The lesion is described as fluid-filled and raised or bumpy; the patient is 18–29, female; reported duration is one to four weeks; located on the leg; reported lesion symptoms include itching, bothersome appearance and pain; the patient considered this a rash; close-up view; the patient also reports fever — 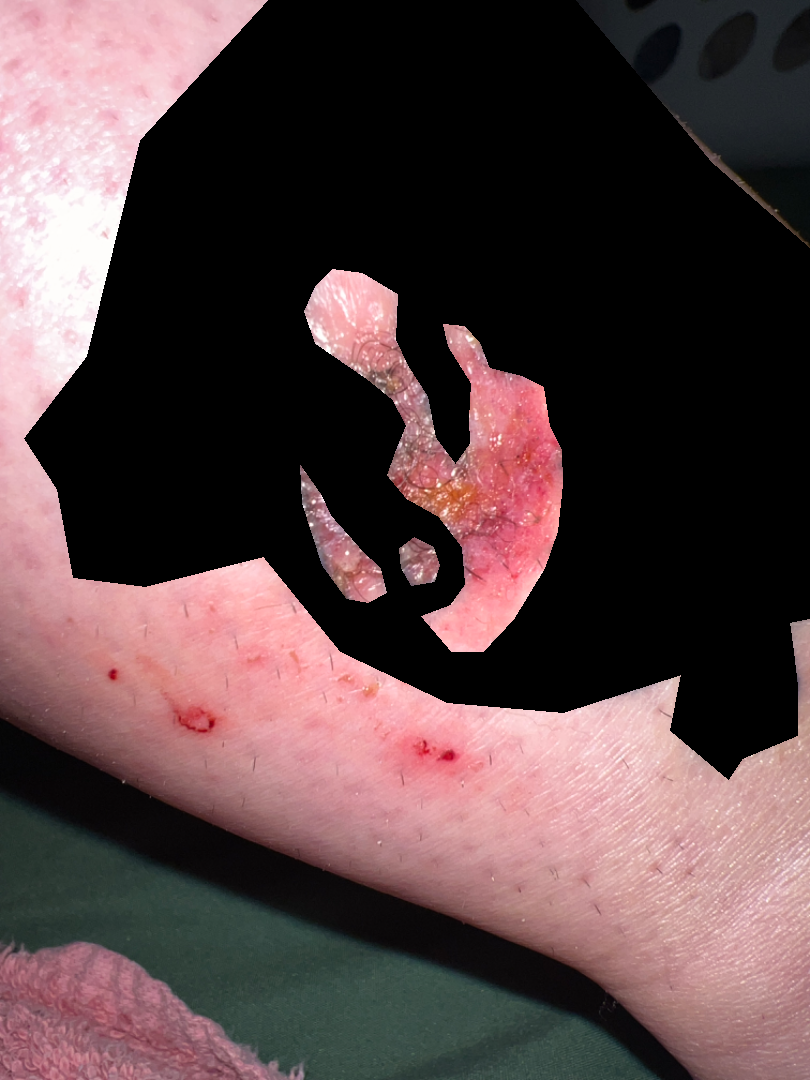The skin condition could not be confidently assessed from this image.